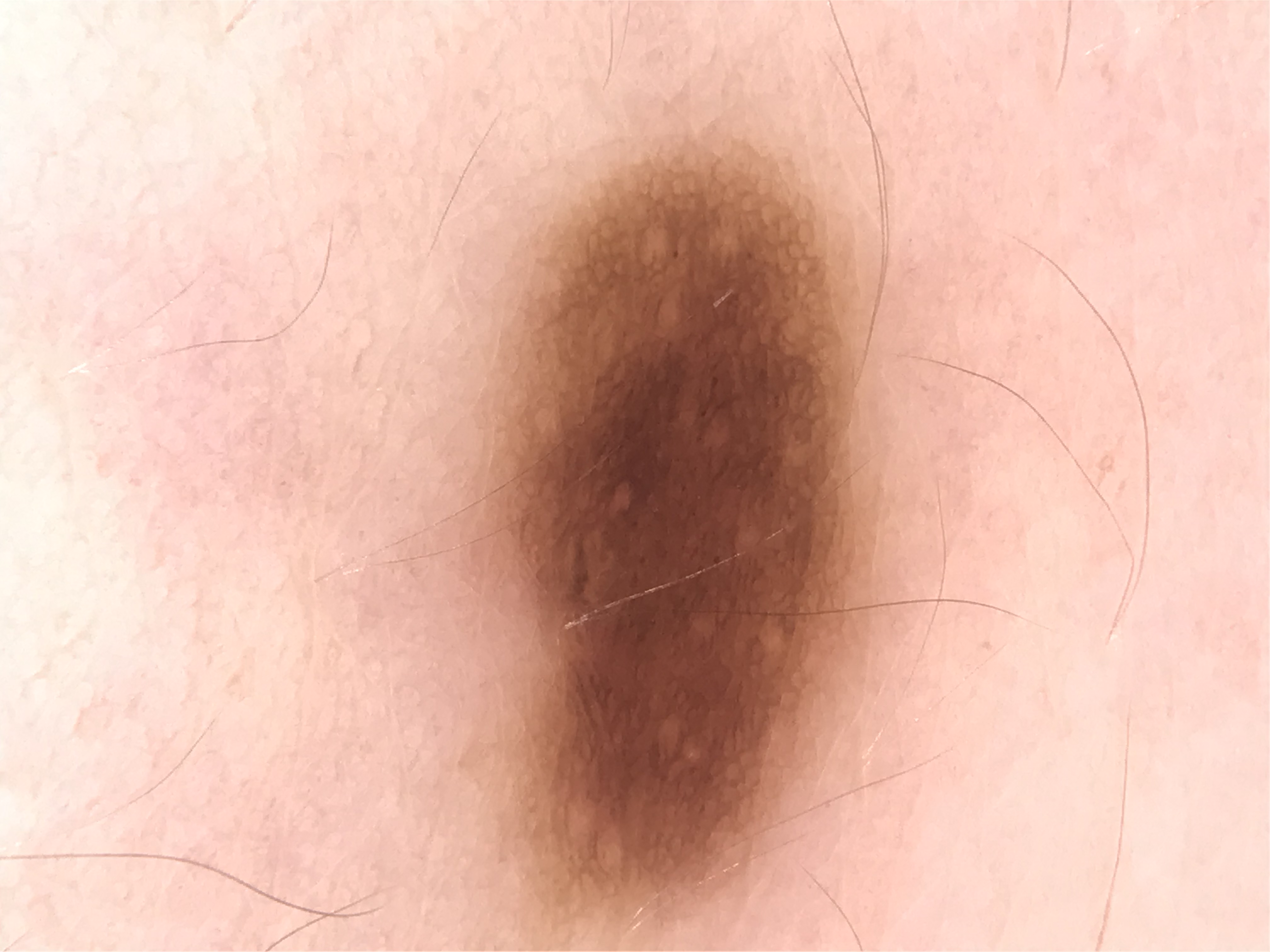Case:
A dermoscopic close-up of a skin lesion.
Conclusion:
Diagnosed as a dysplastic junctional nevus.